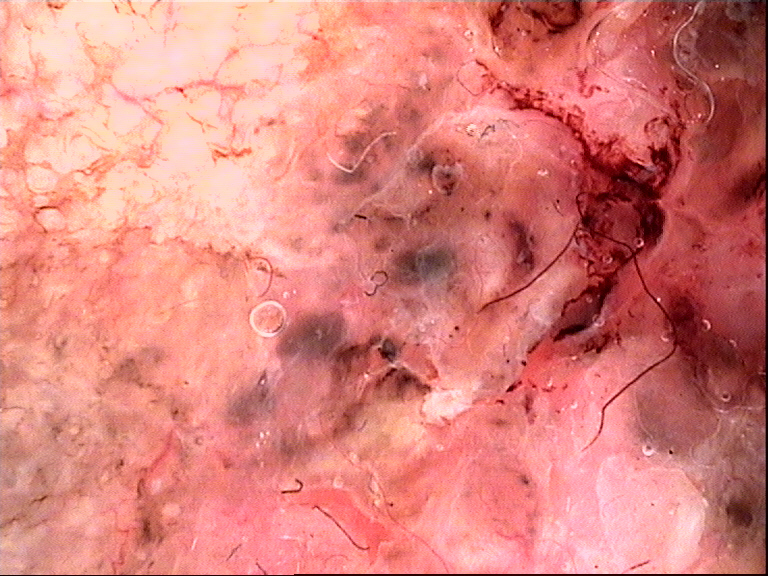A dermoscopic image of a skin lesion. The morphology is that of a keratinocytic lesion. The biopsy diagnosis was a basal cell carcinoma.